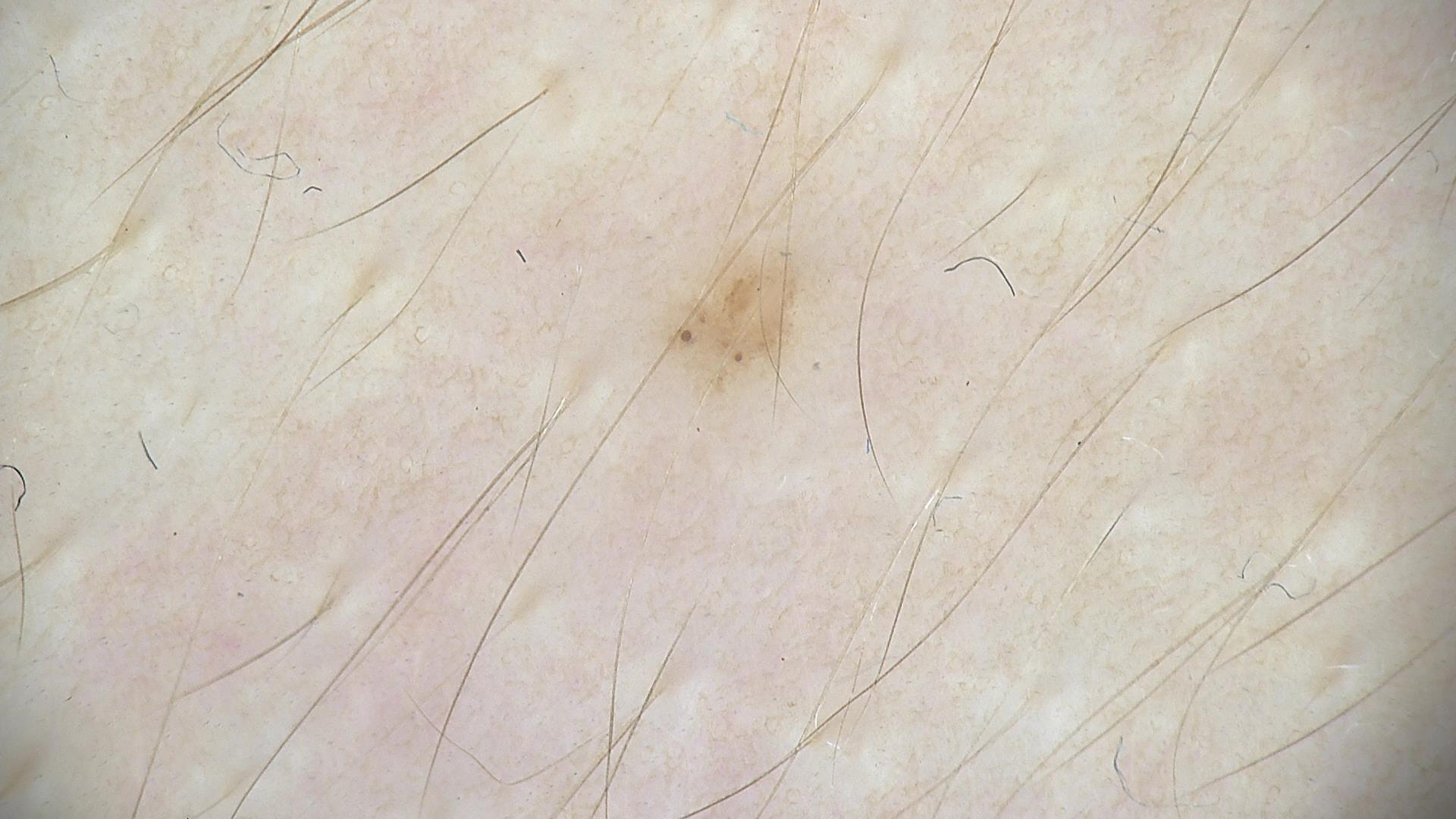Consistent with a dysplastic junctional nevus.